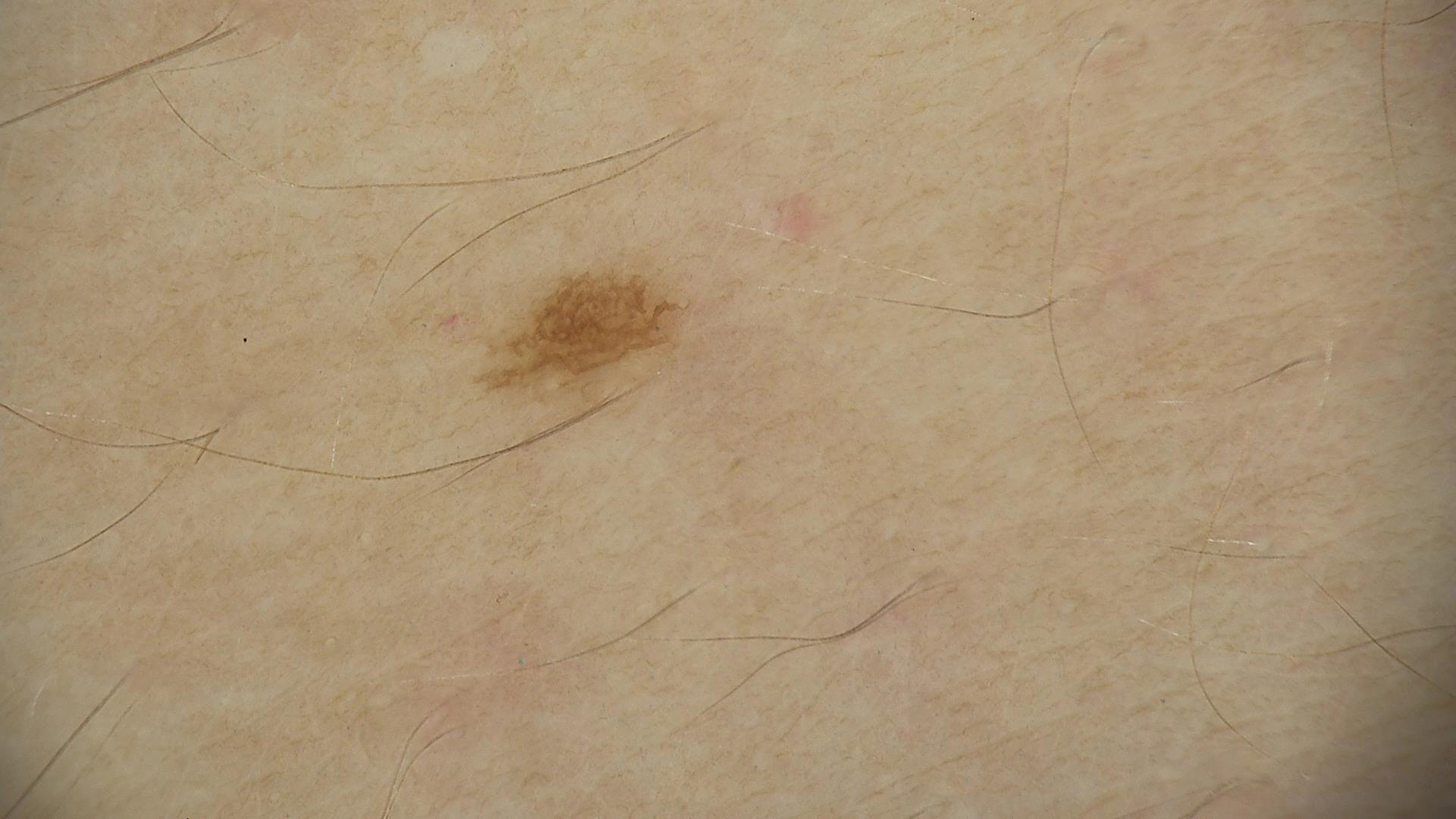assessment = junctional nevus (expert consensus).